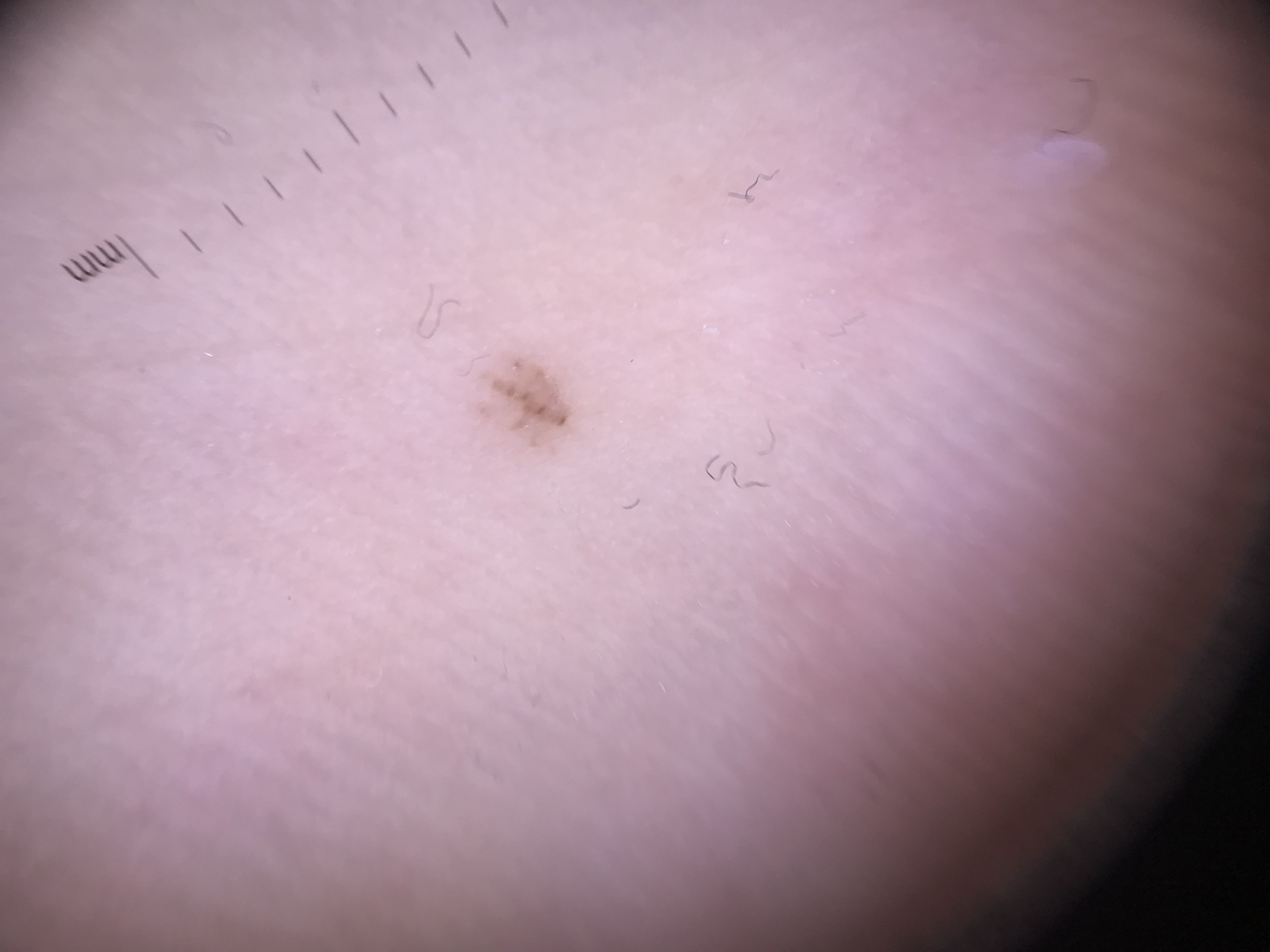lesion type: banal; assessment: acral junctional nevus (expert consensus).